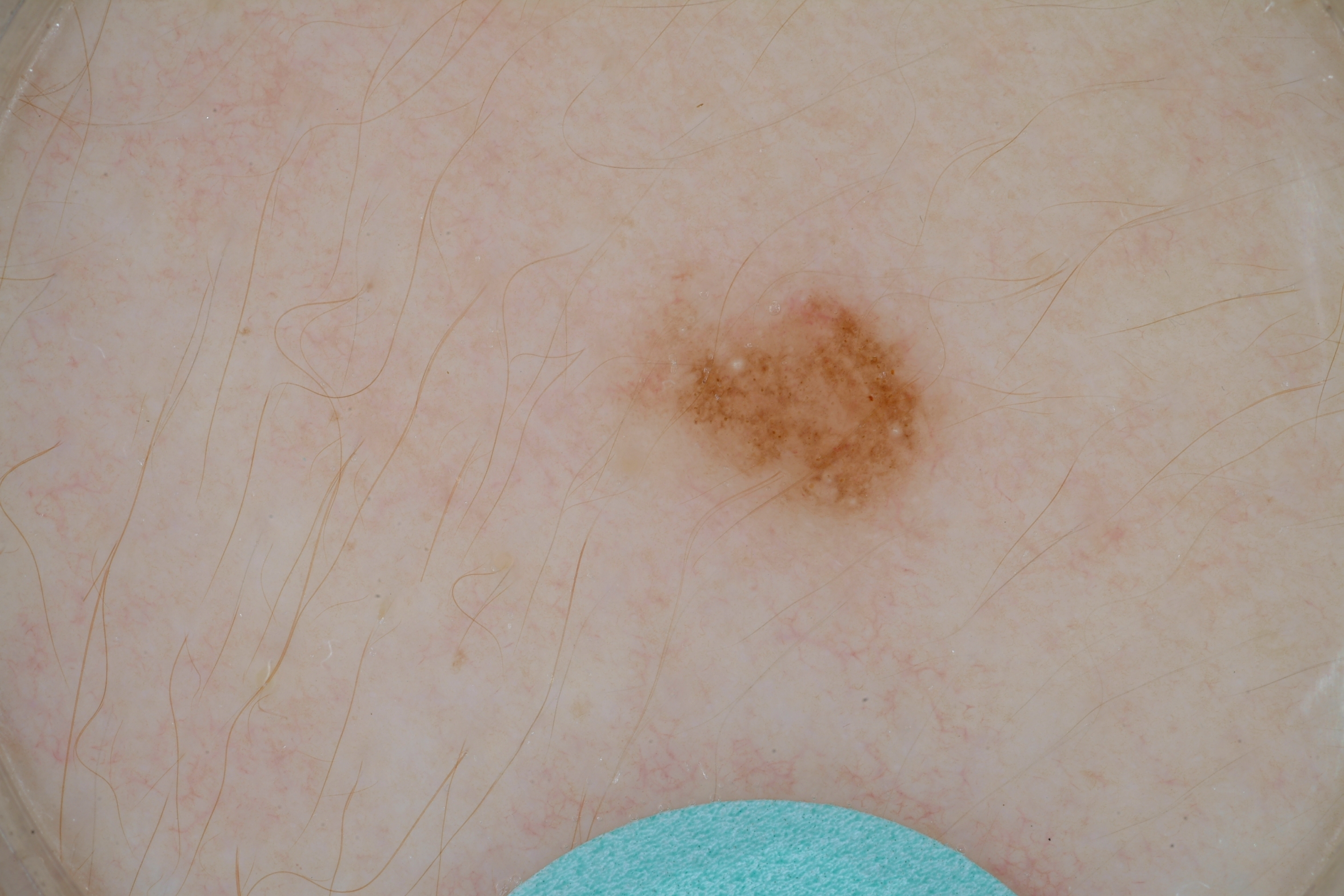A dermoscopic view of a skin lesion. A female subject aged 13-17. In (x1, y1, x2, y2) order, the lesion spans (610, 261, 962, 545). On dermoscopy, the lesion shows globules, pigment network, and milia-like cysts. Consistent with a melanocytic nevus.